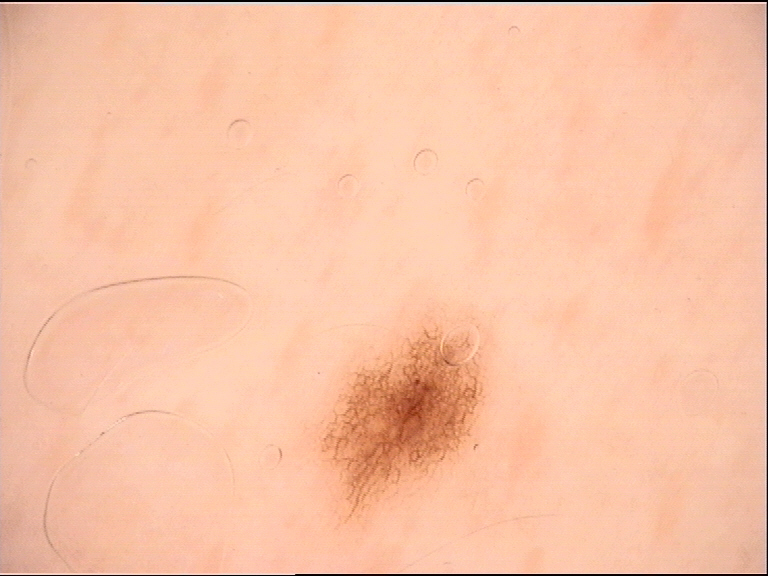The diagnostic label was a dysplastic junctional nevus.